A dermoscopy image of a single skin lesion; a female subject aged around 30:
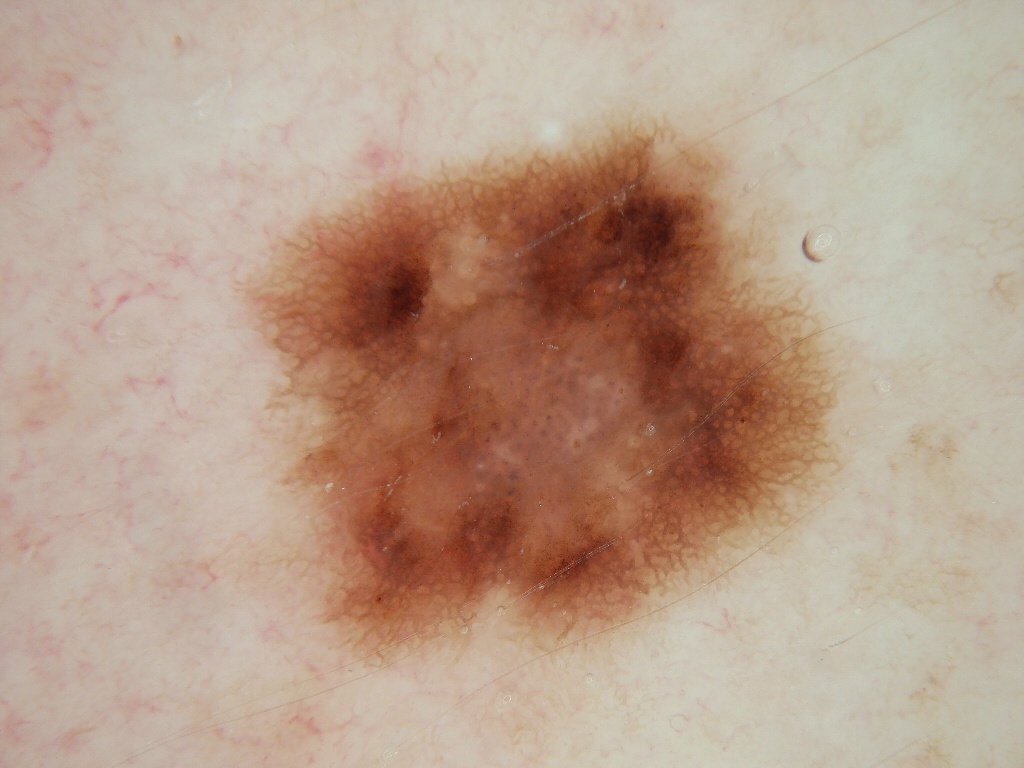The lesion's extent is 241 120 839 667. Dermoscopy demonstrates milia-like cysts, globules, and pigment network. A large lesion occupying much of the field. Clinically diagnosed as a melanocytic nevus, a benign lesion.